Human graders estimated Monk Skin Tone 6 (US pool) or 4 (India pool). Reported duration is one to three months. The arm is involved. The lesion is described as rough or flaky. The patient considered this a rash. This image was taken at an angle. The lesion is associated with bothersome appearance, enlargement and itching:
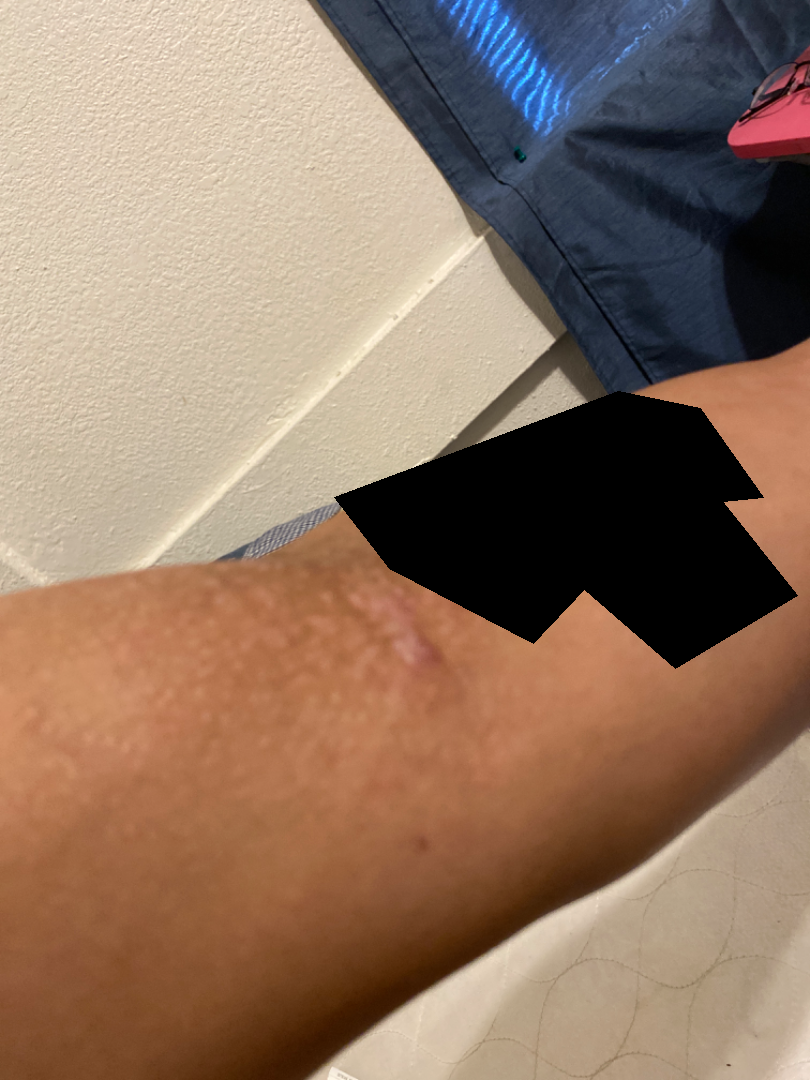On remote review of the image, the reviewer's impression was Eczema.